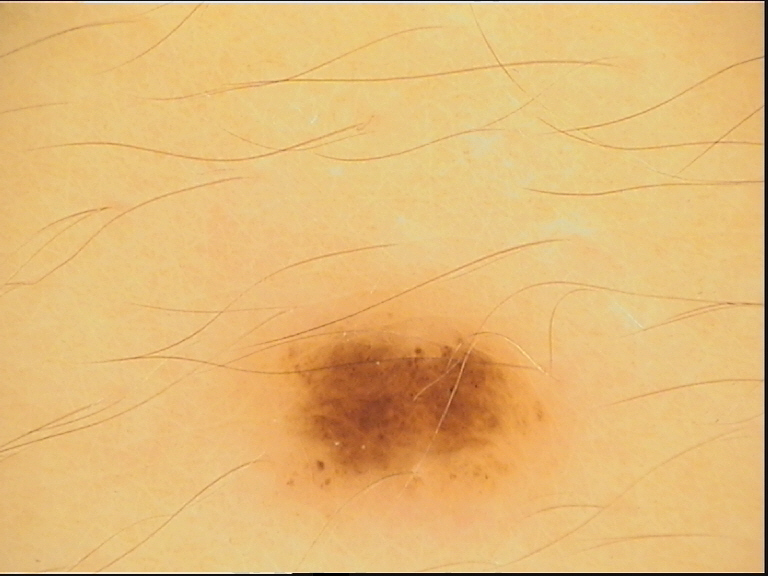A dermoscopic image of a skin lesion.
Consistent with a dysplastic junctional nevus.